Dermoscopy of a skin lesion.
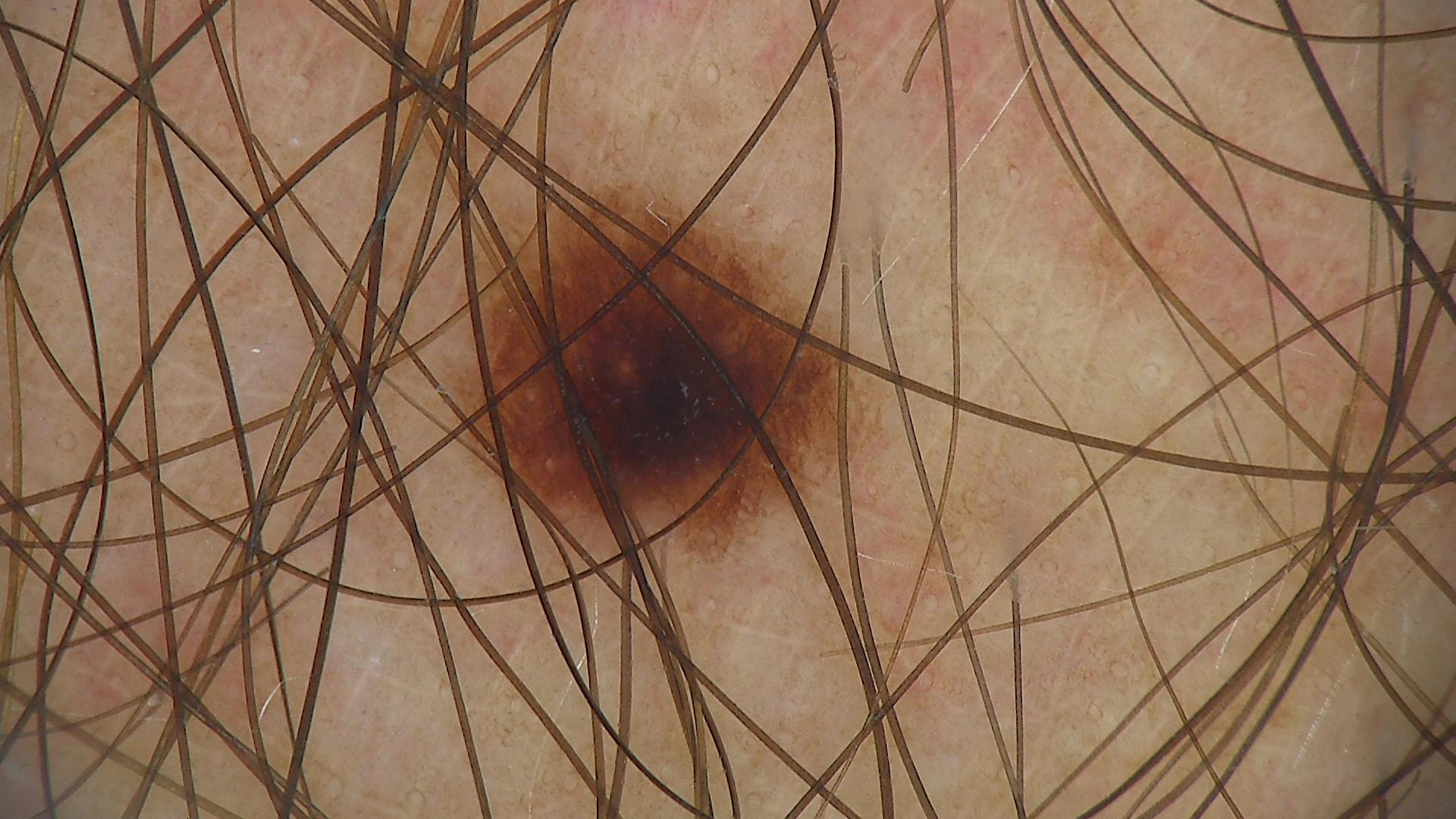Classified as a dysplastic junctional nevus.